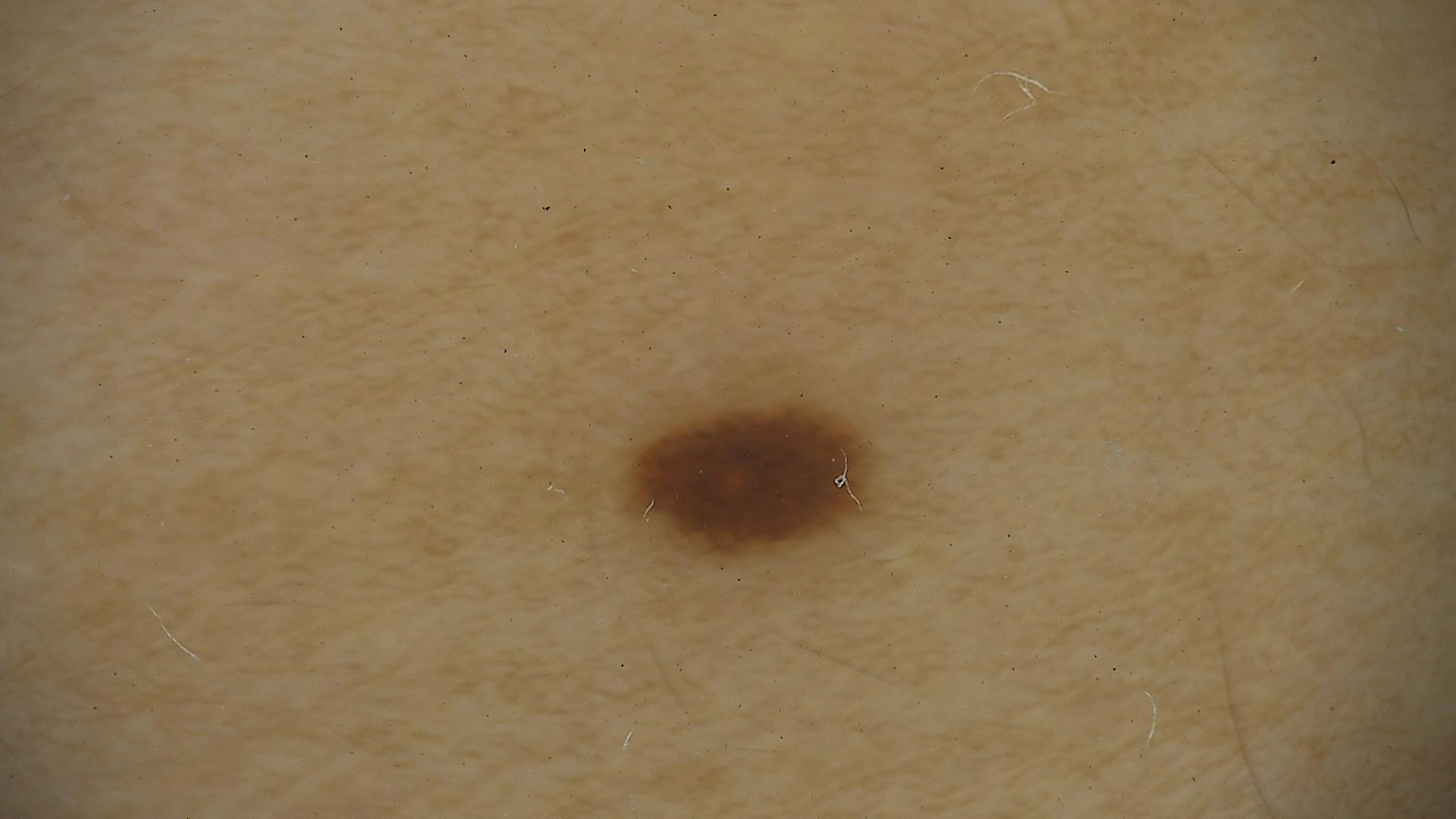Case:
- class — dysplastic junctional nevus (expert consensus)